Dermoscopy of a skin lesion.
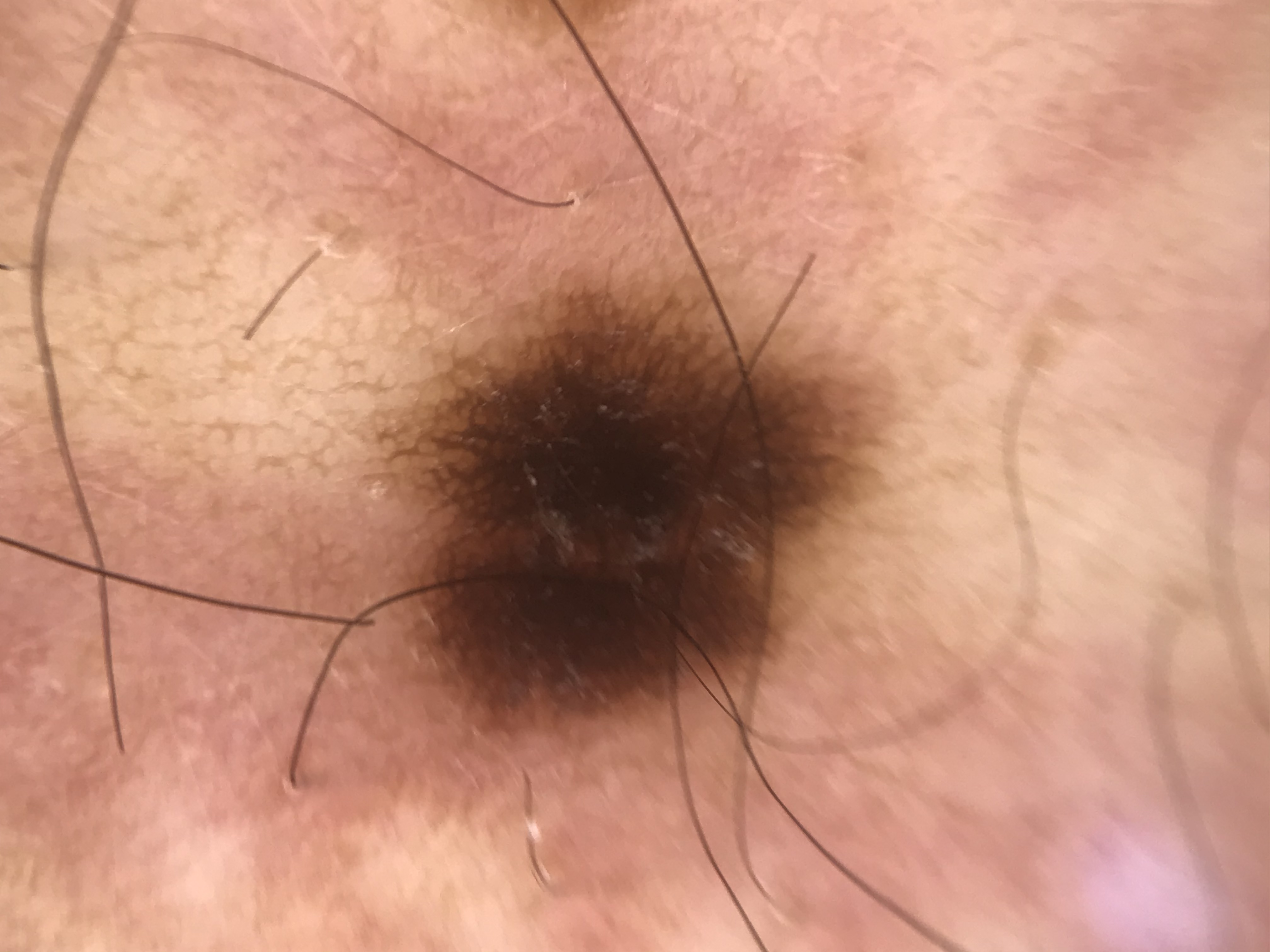The diagnostic label was a banal lesion — a junctional nevus.